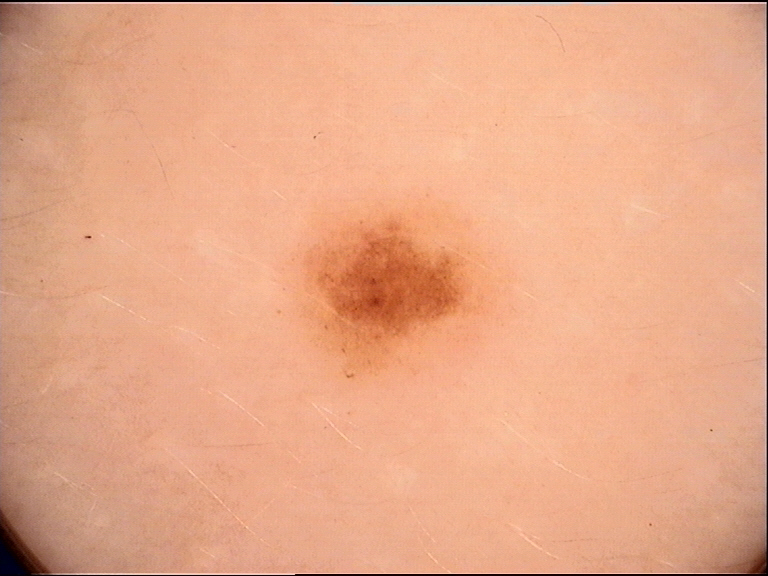imaging — dermoscopy
diagnosis — junctional nevus (expert consensus)